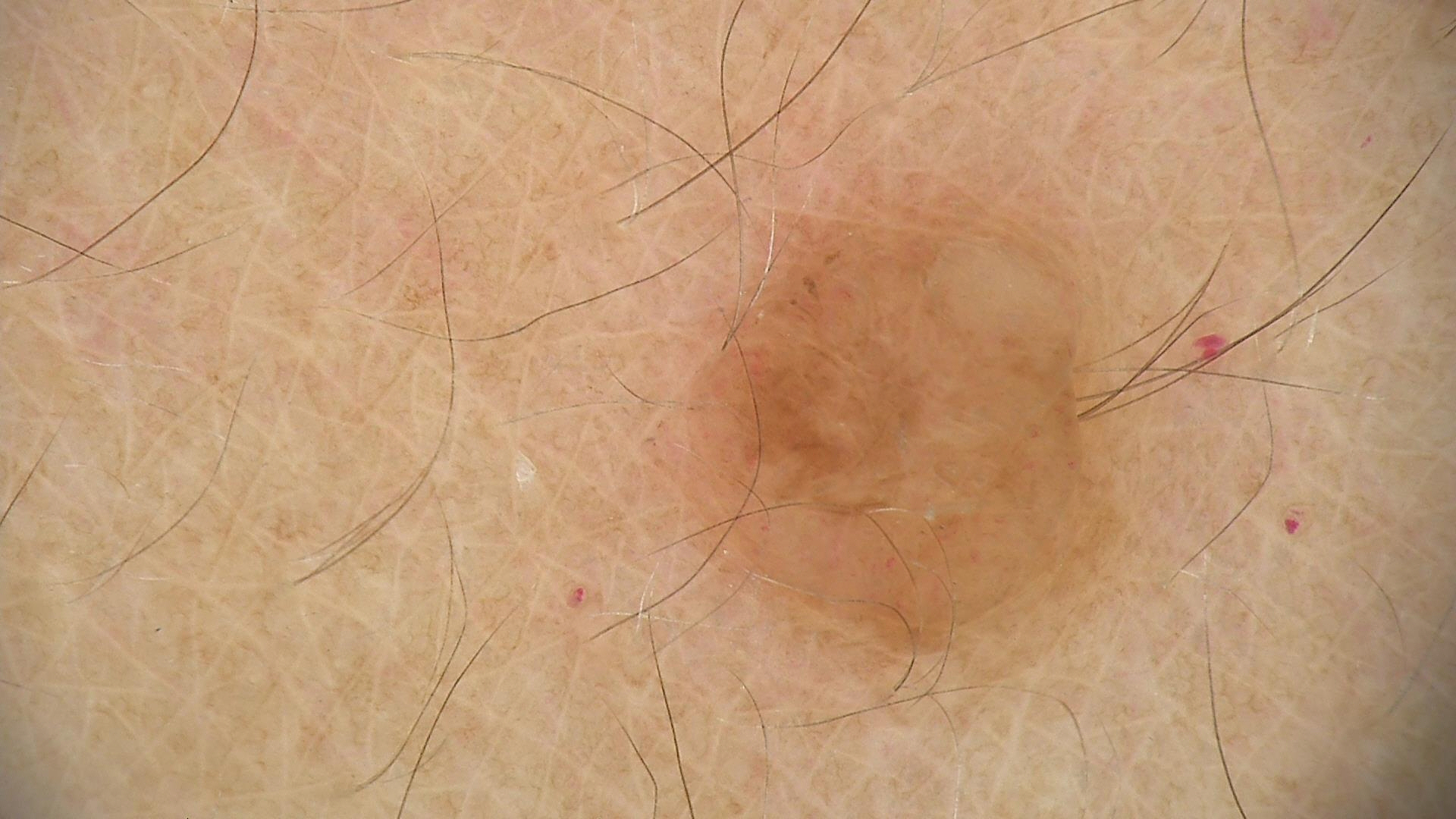modality = dermoscopy
diagnostic label = dermal nevus (expert consensus)